The affected area is the back of the hand, arm, back of the torso and front of the torso · the patient is 50–59, female · the photograph is a close-up of the affected area.
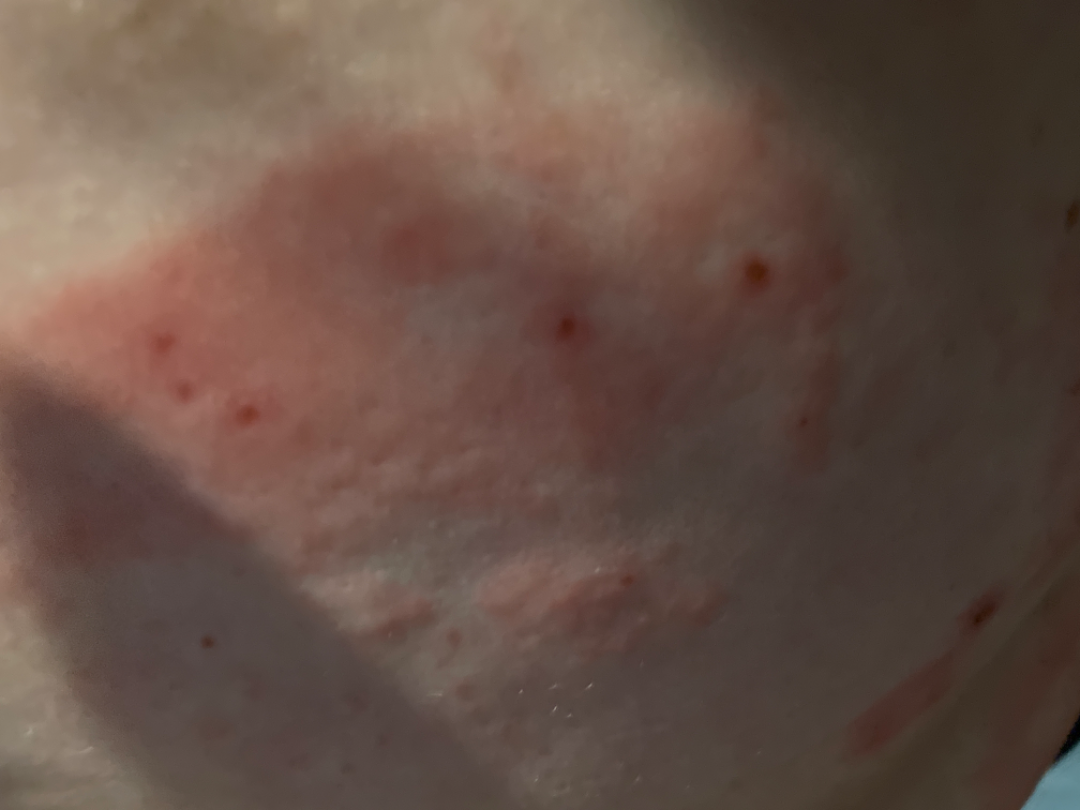The reviewing dermatologist was unable to assign a differential diagnosis from the image.